A female patient aged 92 — 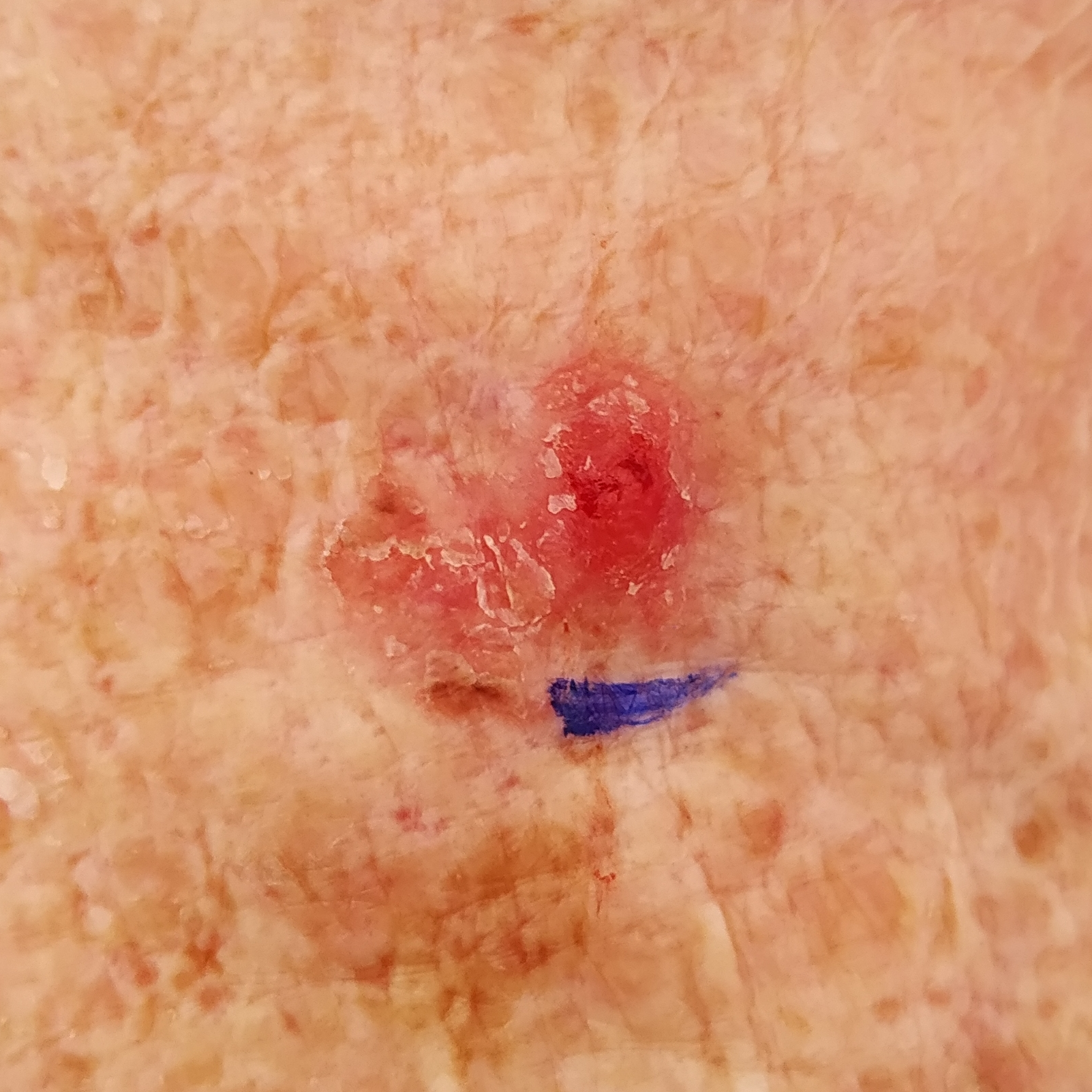Q: What are the lesion's dimensions?
A: 20 × 15 mm
Q: What does the patient describe?
A: itching, bleeding
Q: What is this lesion?
A: squamous cell carcinoma (biopsy-proven)